Present for about one day, this image was taken at an angle, reported lesion symptoms include itching, the arm is involved, the patient notes the lesion is raised or bumpy, self-categorized by the patient as a rash — 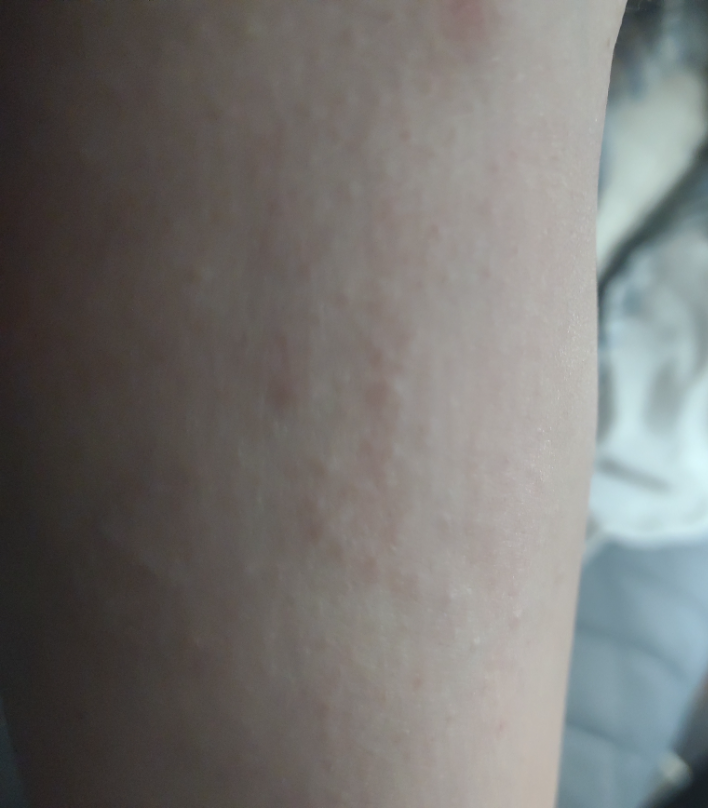No differential diagnosis could be assigned on photographic review.